A dermoscopic close-up of a skin lesion.
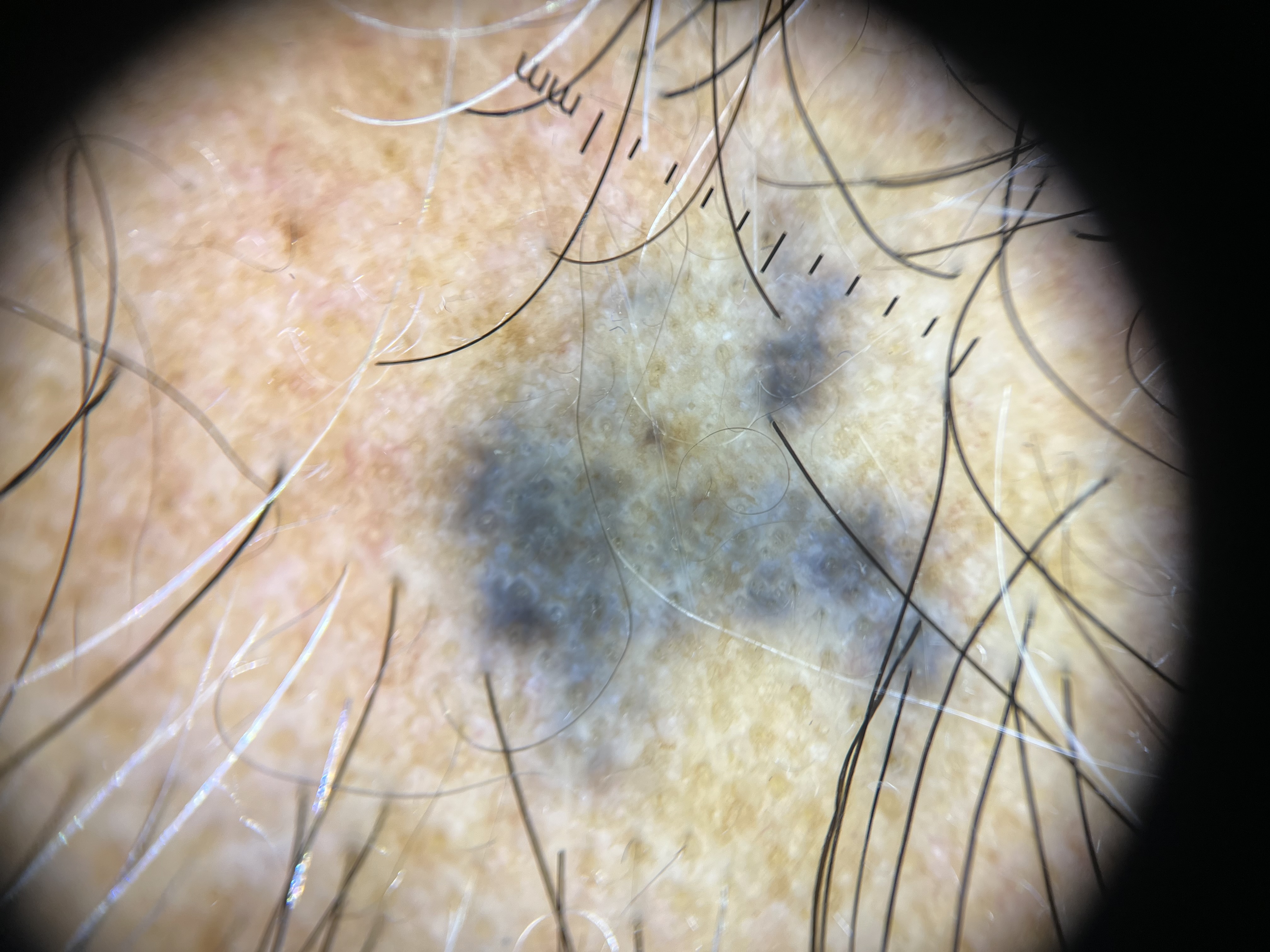assessment = blue nevus (expert consensus)